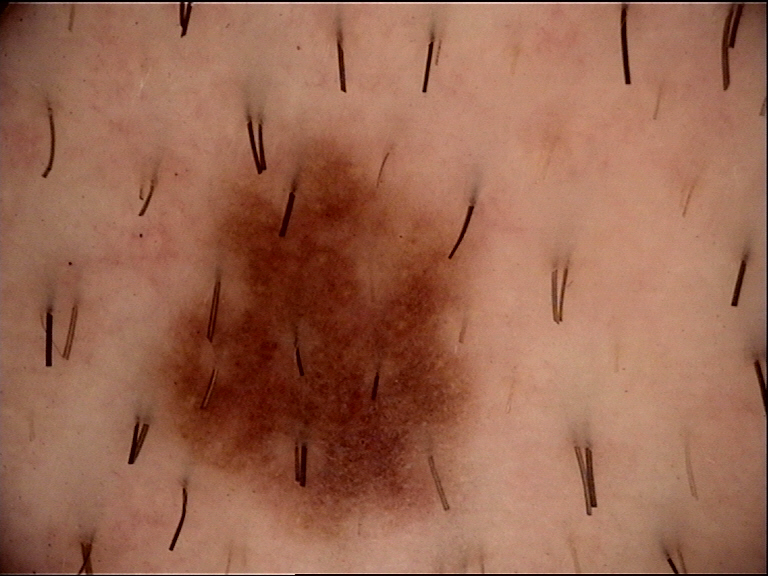Labeled as a dysplastic junctional nevus.